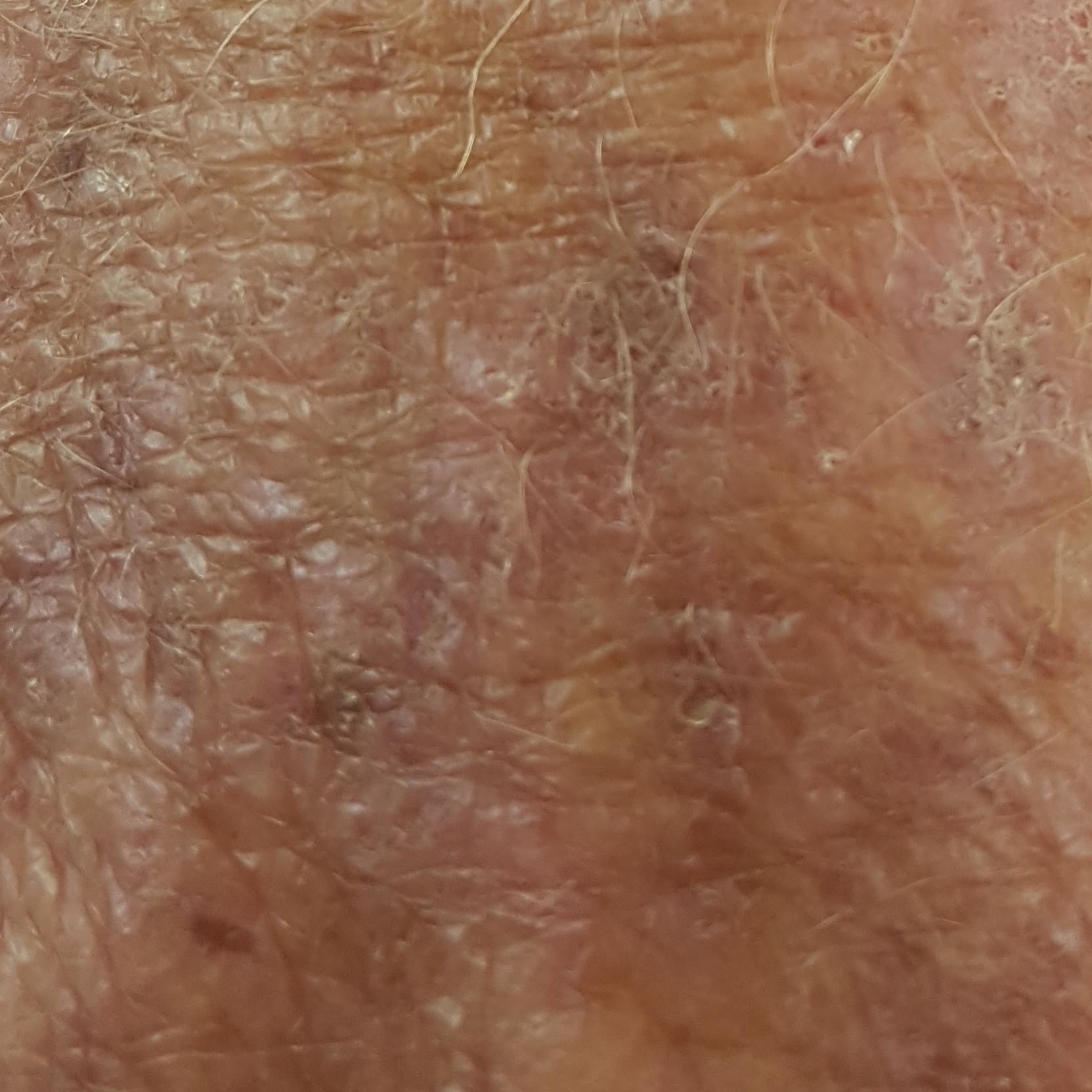- subject — age 31
- imaging — clinical photo
- region — a hand
- patient-reported symptoms — itching / no bleeding, no growth
- assessment — actinic keratosis (clinical consensus)